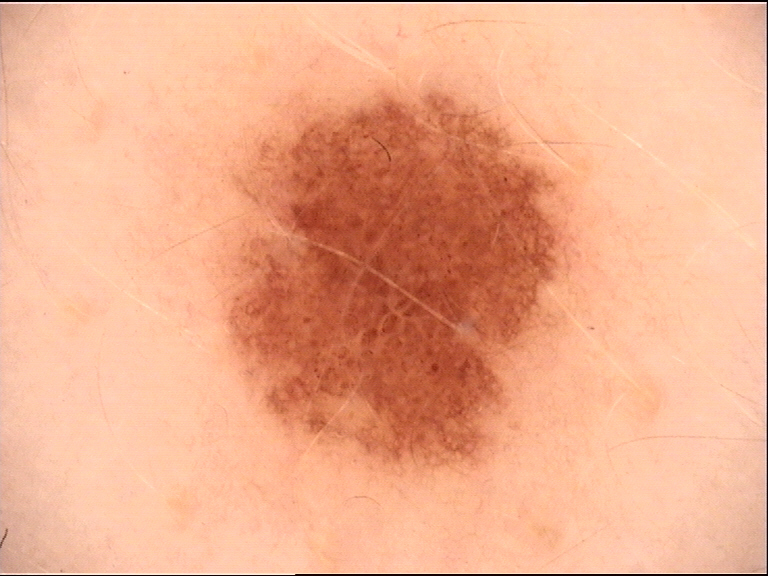label: junctional nevus (expert consensus).